A dermoscopy image of a single skin lesion: 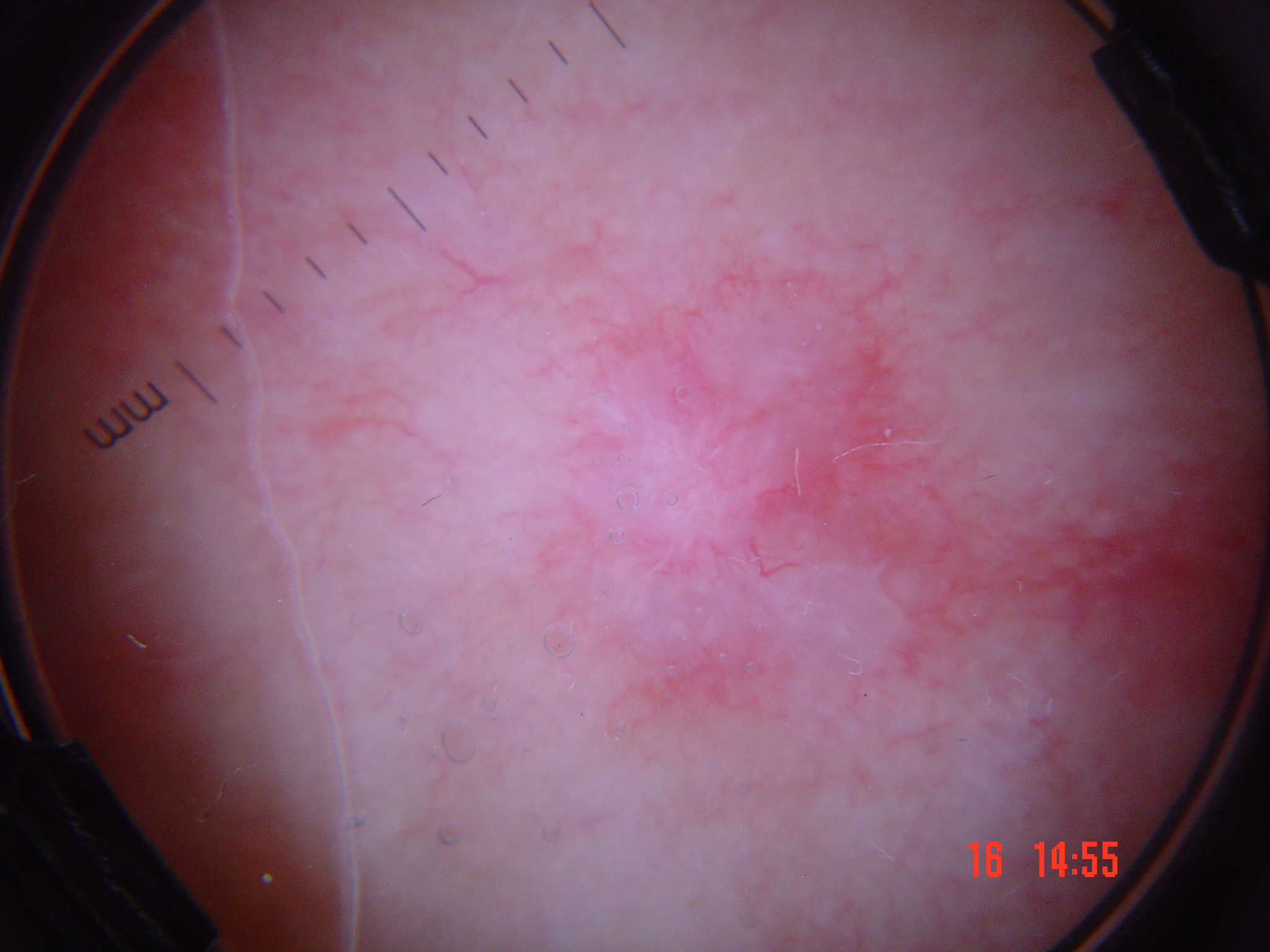classification: keratinocytic | class: squamous cell carcinoma (biopsy-proven).